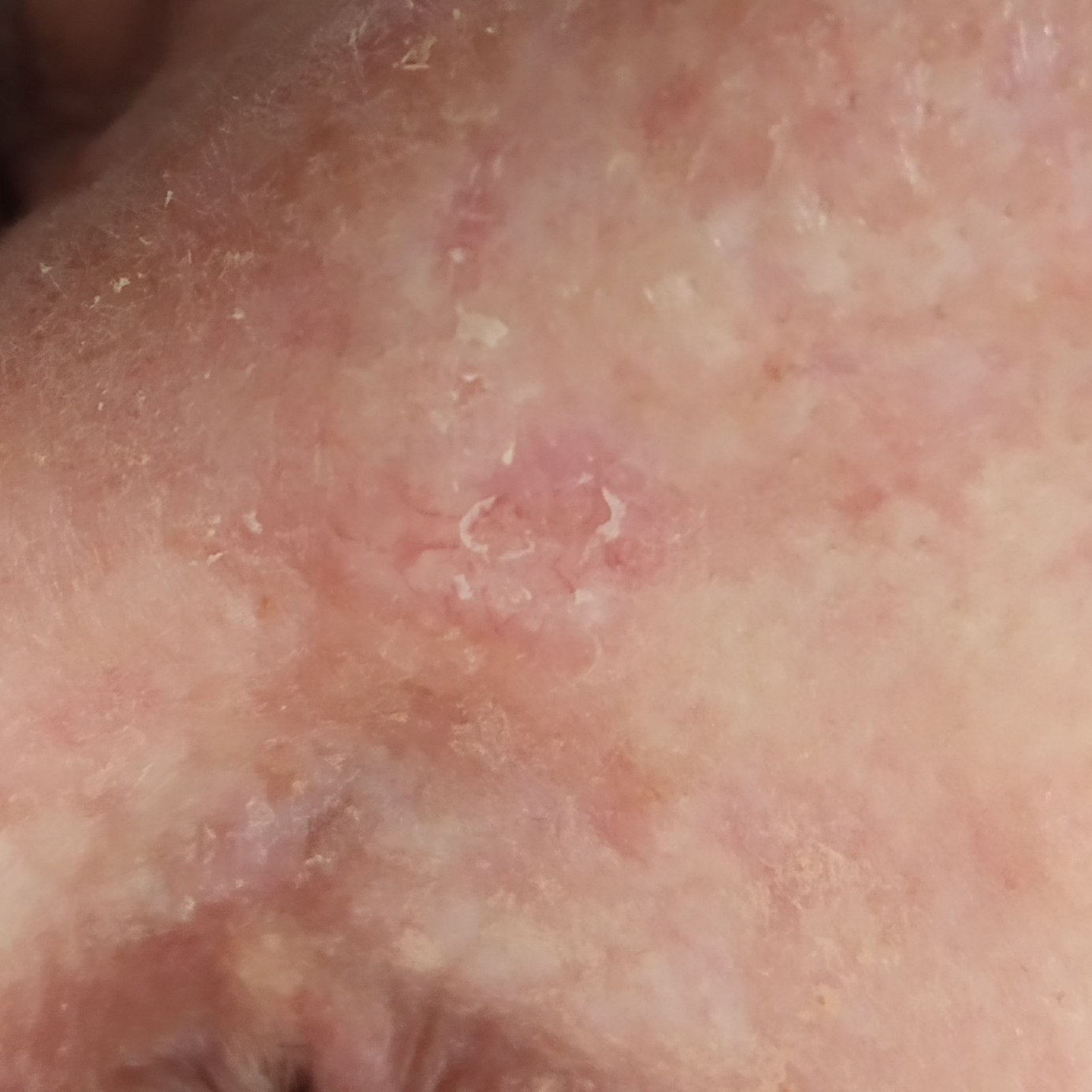By history, prior skin cancer (patient or family) and prior malignancy (patient or family). A female subject age 64. The patient was assessed as Fitzpatrick phototype II. A clinical photograph of a skin lesion. The lesion is located on the nose. The lesion measures 7 × 5 mm. By the patient's account, the lesion is elevated and itches. Confirmed on histopathology as a malignancy — a basal cell carcinoma.